The photograph was taken at an angle — 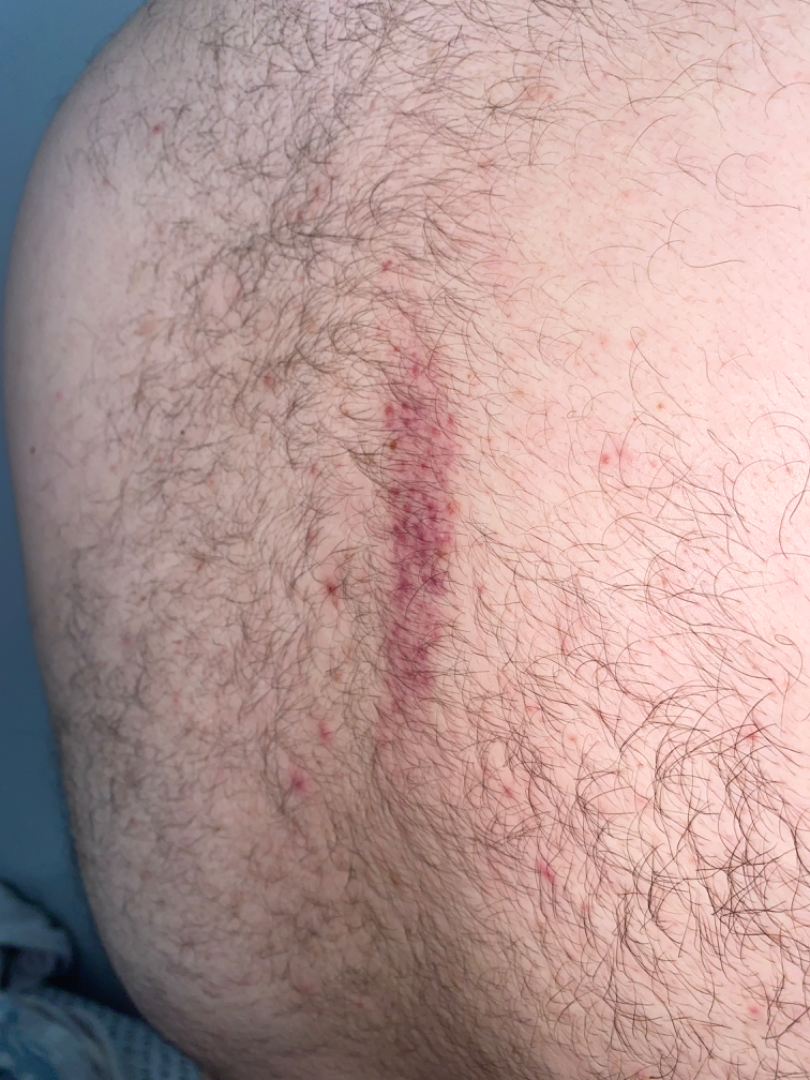The reviewing clinician's impression was: the differential includes Abrasion, scrape, or scab; Benign cutaneous vascular tumor; and ecchymoses, with no clear leading consideration.